A clinical photograph of a skin lesion. Skin type III:
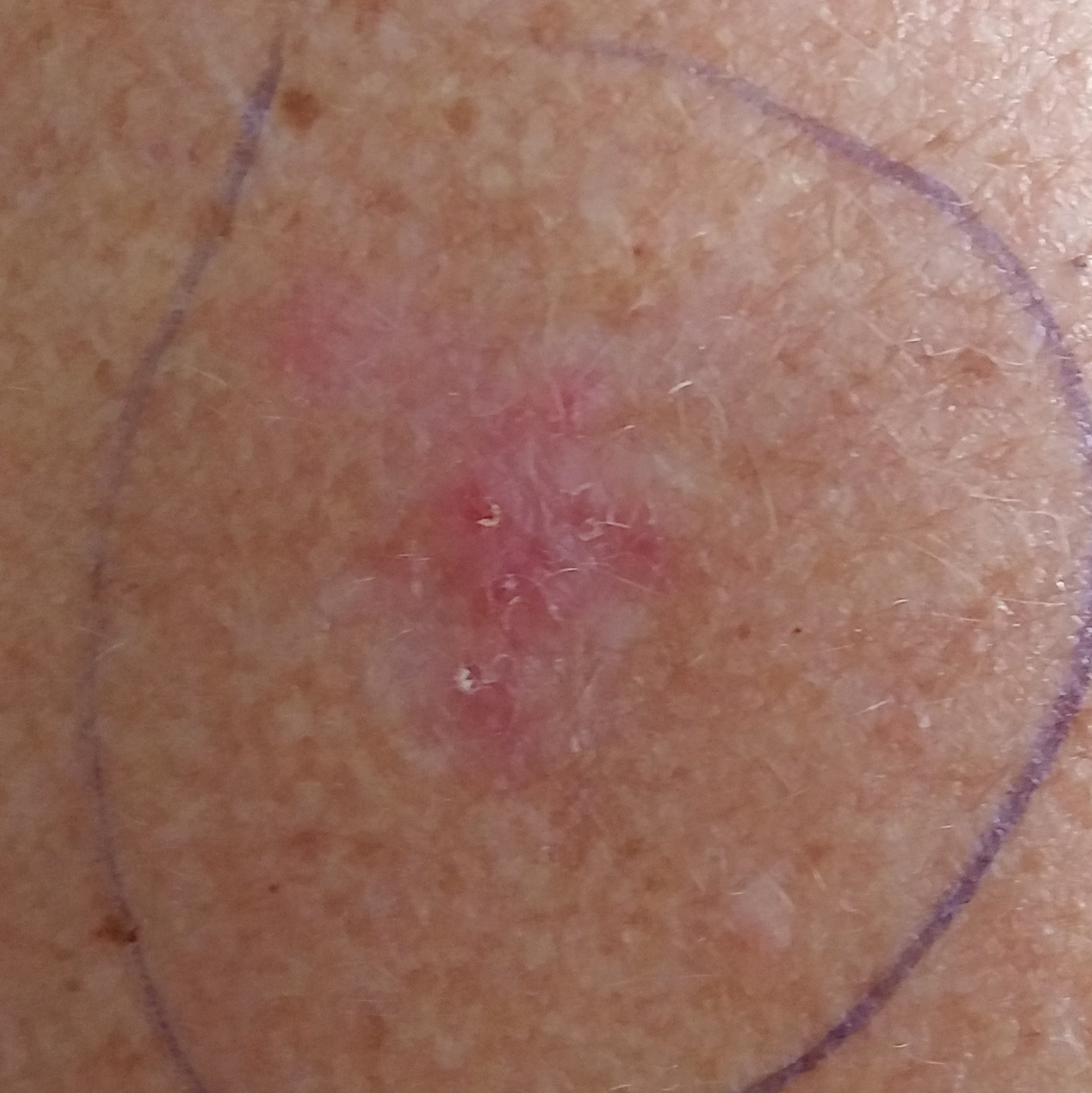Located on the chest. On biopsy, the diagnosis was a basal cell carcinoma.